A dermatoscopic image of a skin lesion; a female patient aged 38 to 42 — 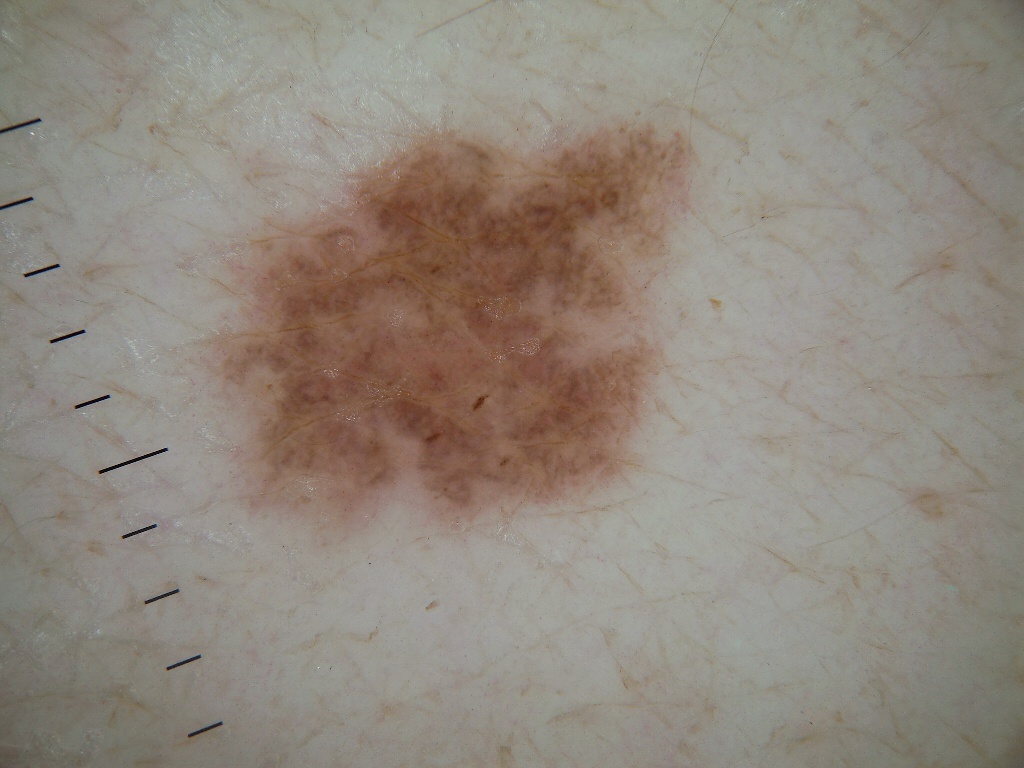A moderately sized lesion.
The dermoscopic pattern shows pigment network.
The lesion is bounded by (215, 122, 689, 526).
Diagnosed as a melanocytic nevus, a benign skin lesion.